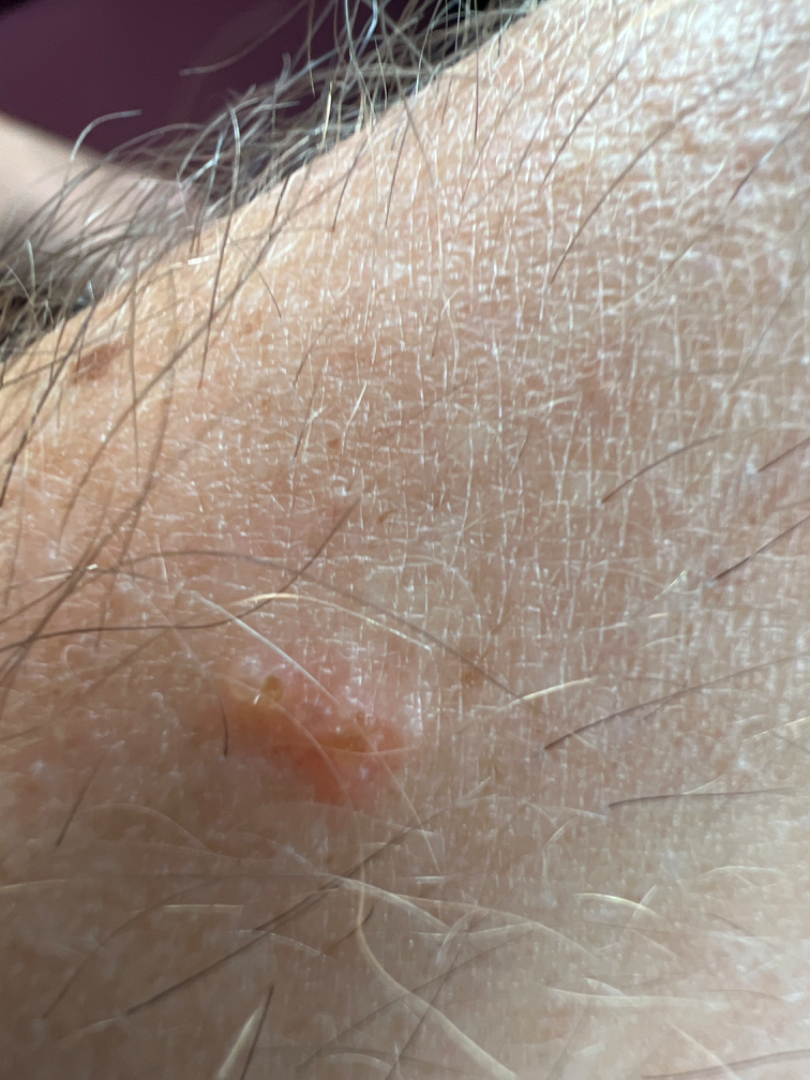Q: Could the case be diagnosed?
A: could not be assessed
Q: What is the framing?
A: close-up
Q: Reported symptoms?
A: itching
Q: Texture?
A: raised or bumpy
Q: How does the patient describe it?
A: a rash
Q: Where on the body?
A: leg and arm